A skin lesion imaged with a dermatoscope: 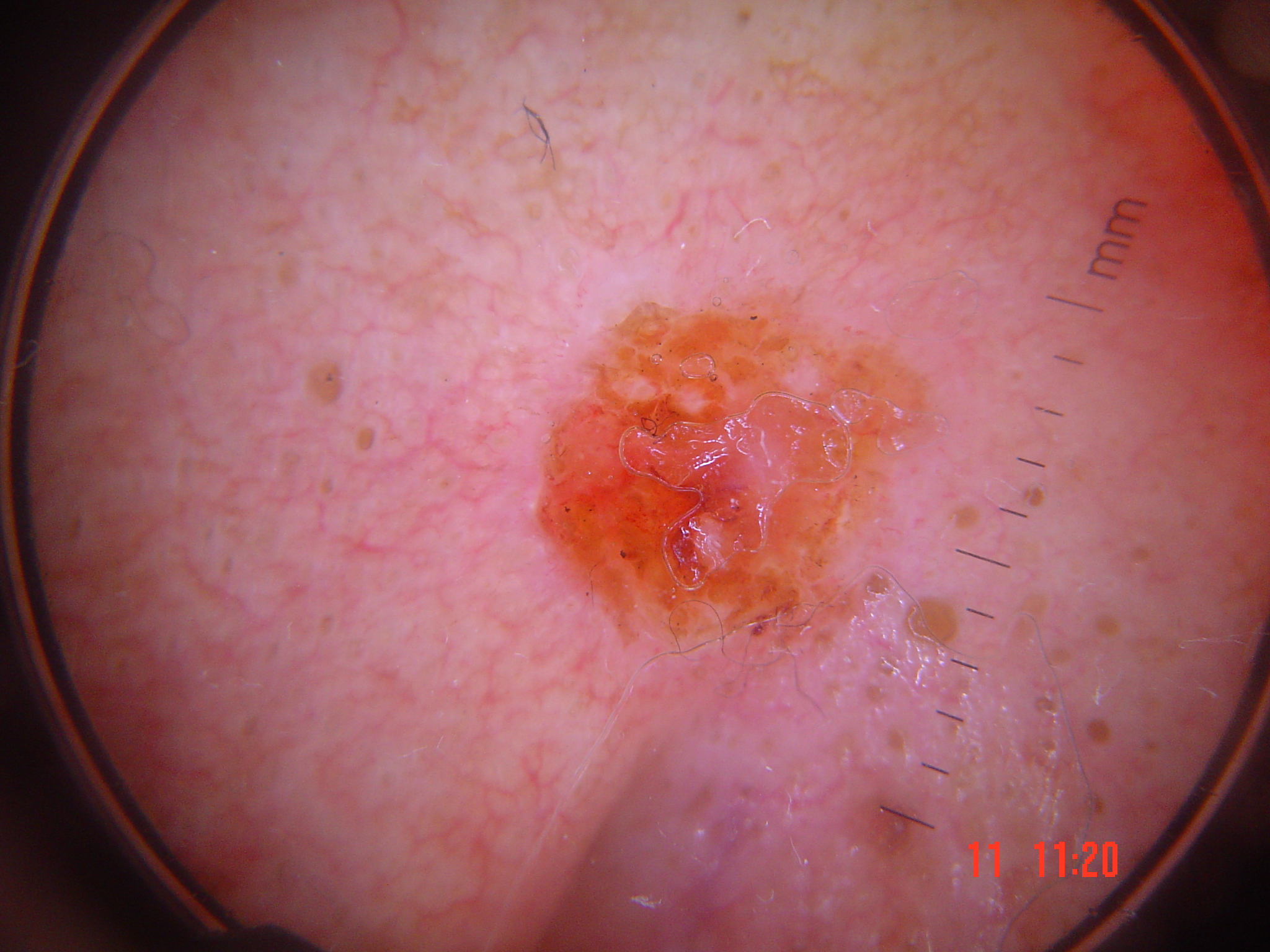The morphology is that of a keratinocytic lesion. Biopsy-confirmed as a squamous cell carcinoma.